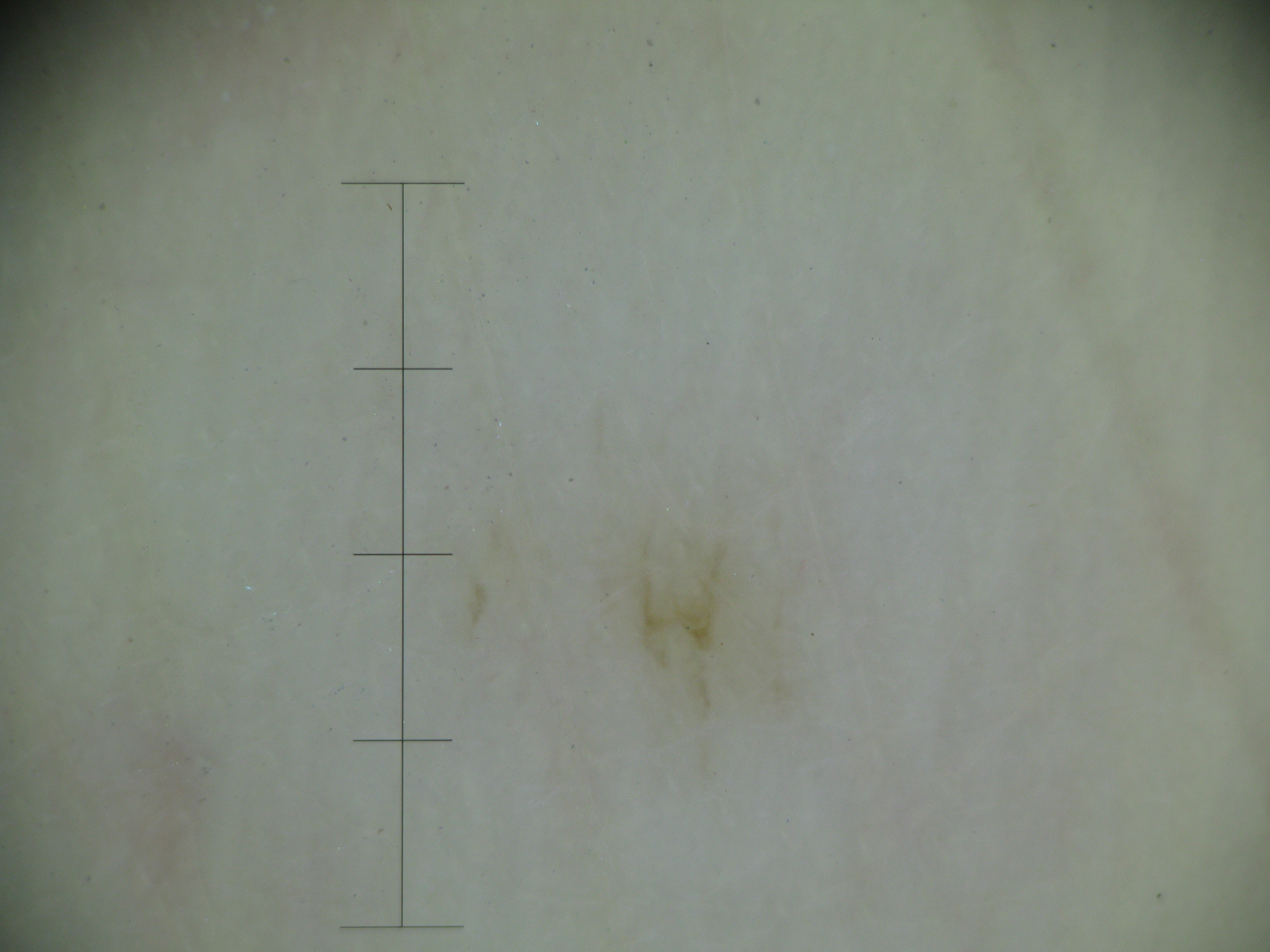Summary: A skin lesion imaged with a dermatoscope. Impression: Classified as a banal lesion — an acral junctional nevus.